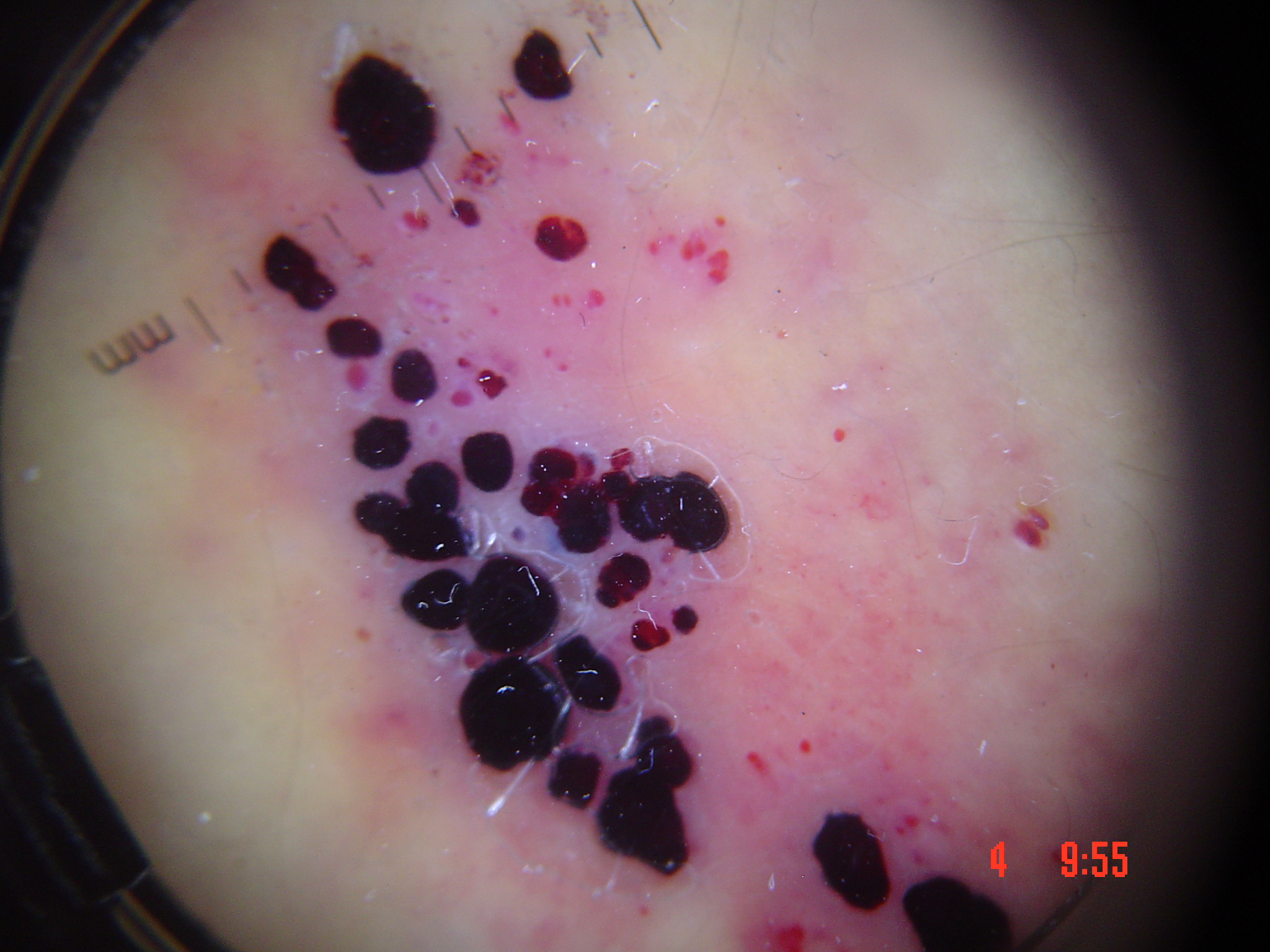{
  "diagnosis": {
    "name": "angiokeratoma",
    "code": "angk",
    "malignancy": "benign",
    "super_class": "non-melanocytic",
    "confirmation": "expert consensus"
  }
}